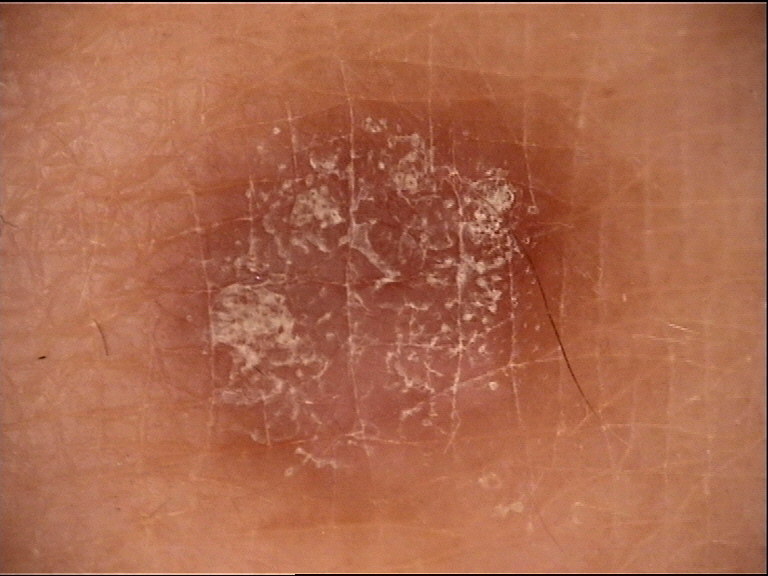Dermoscopy of a skin lesion.
The architecture is that of a fibro-histiocytic lesion.
The diagnosis was a benign lesion — a dermatofibroma.